The patient describes having a moderate number of moles · the patient says their skin reddens painfully with sun exposure · by self-report, no personal history of cancer and no sunbed use · a female patient 50 years of age · a clinical close-up of a skin lesion.
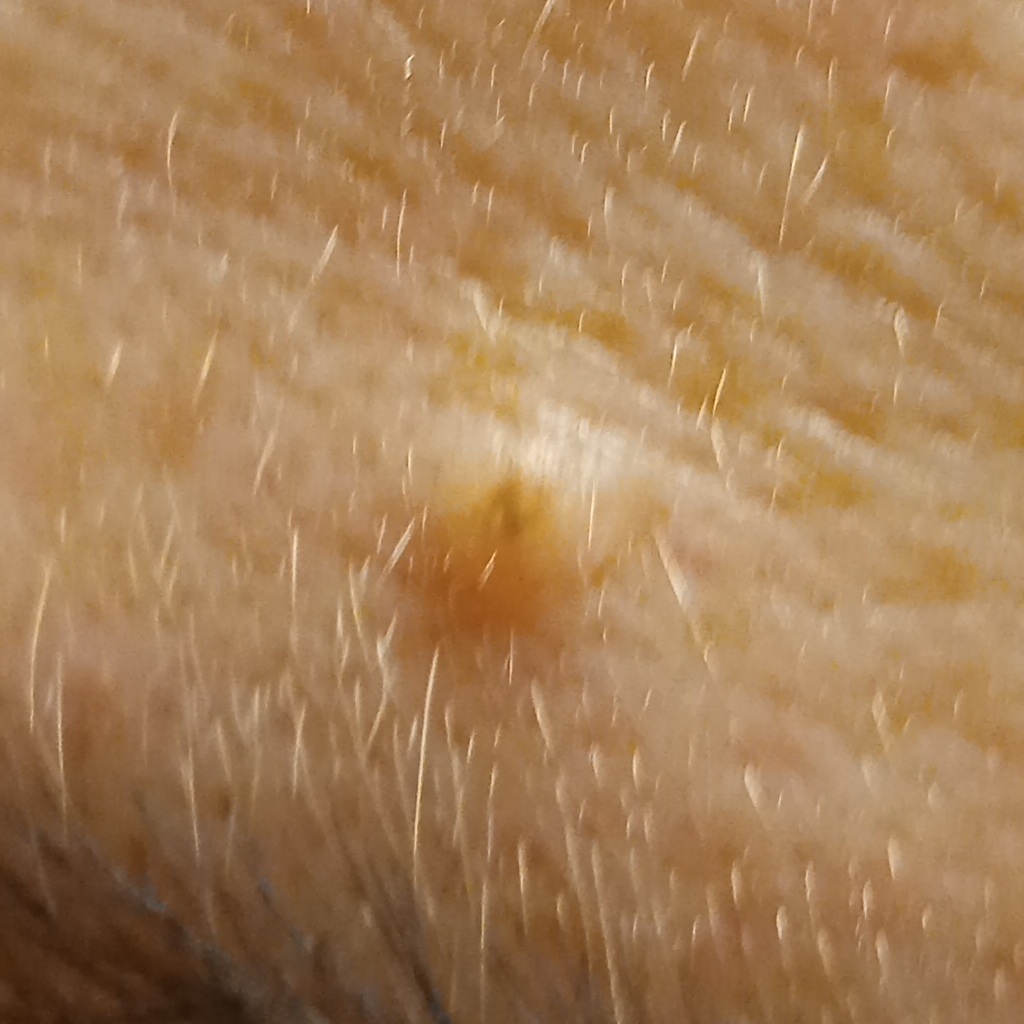| feature | finding |
|---|---|
| site | the face |
| diameter | 1.8 mm |
| diagnosis | melanocytic nevus (dermatologist consensus) |